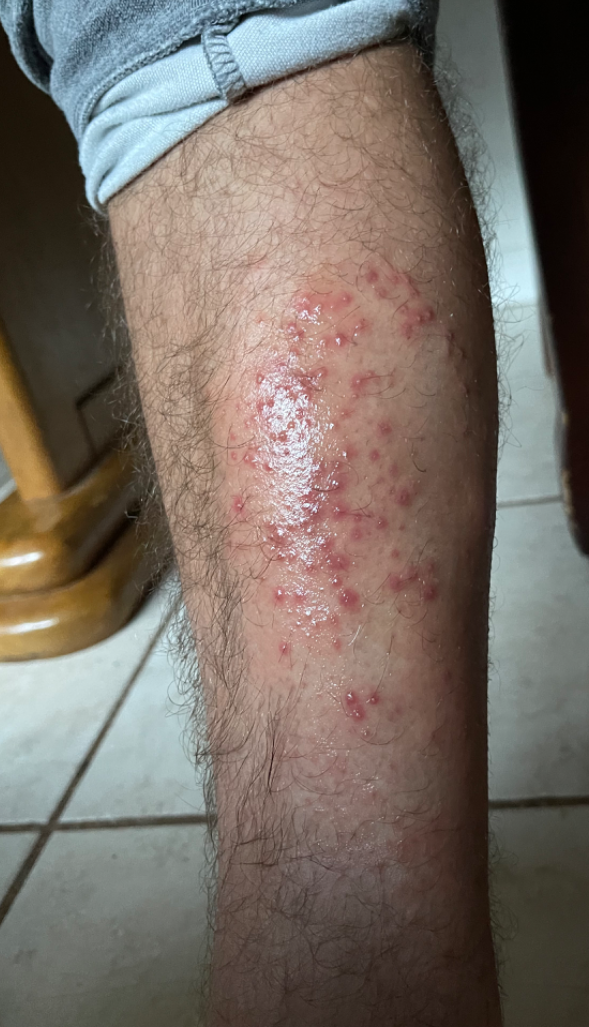On teledermatology review, the impression was split between Insect Bite and Allergic Contact Dermatitis.